A subject 51 years old; a clinical photo of a skin lesion taken with a smartphone:
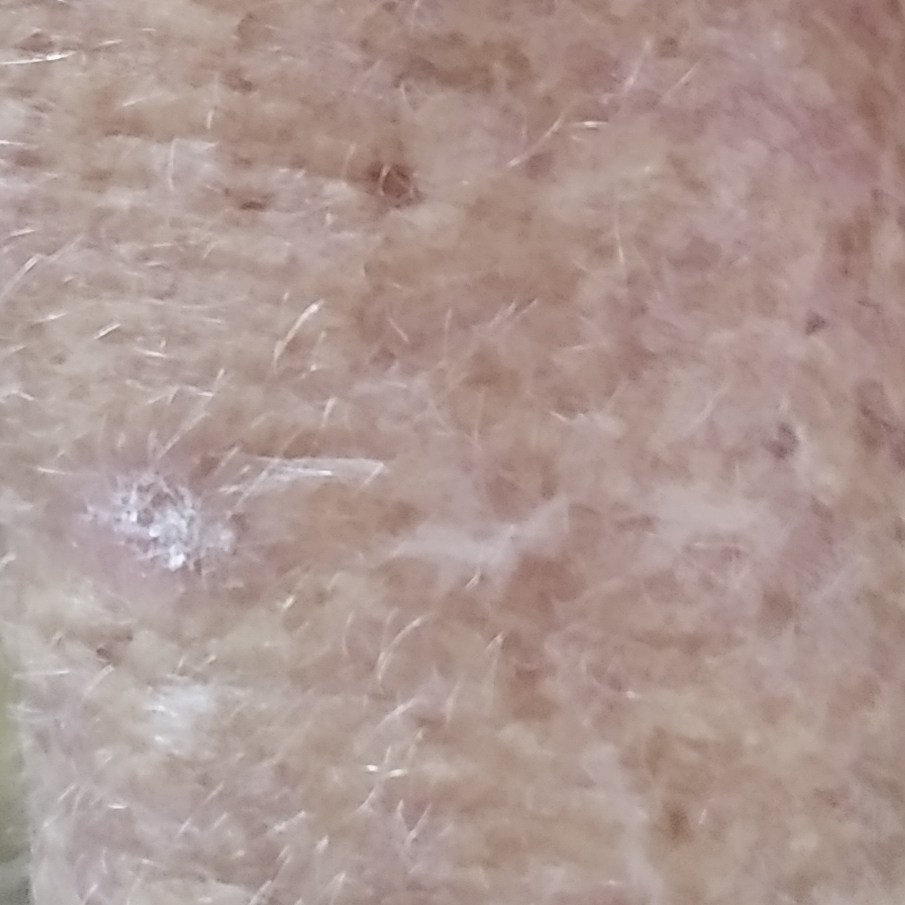{"symptoms": {"present": ["itching"], "absent": ["growth"]}, "diagnosis": {"name": "actinic keratosis", "code": "ACK", "malignancy": "indeterminate", "confirmation": "clinical consensus"}}